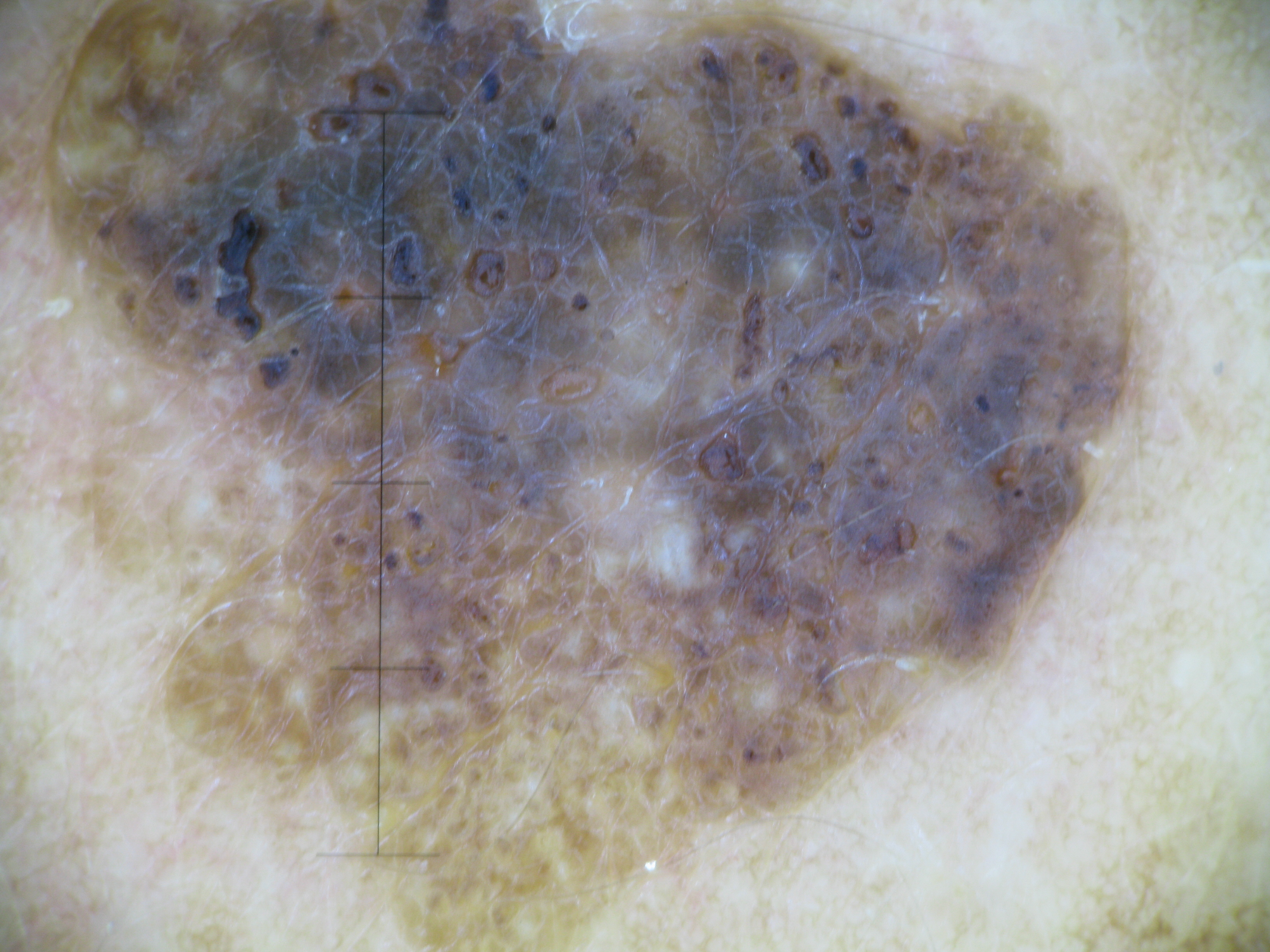Dermoscopy of a skin lesion.
Diagnosed as a keratinocytic lesion — a seborrheic keratosis.